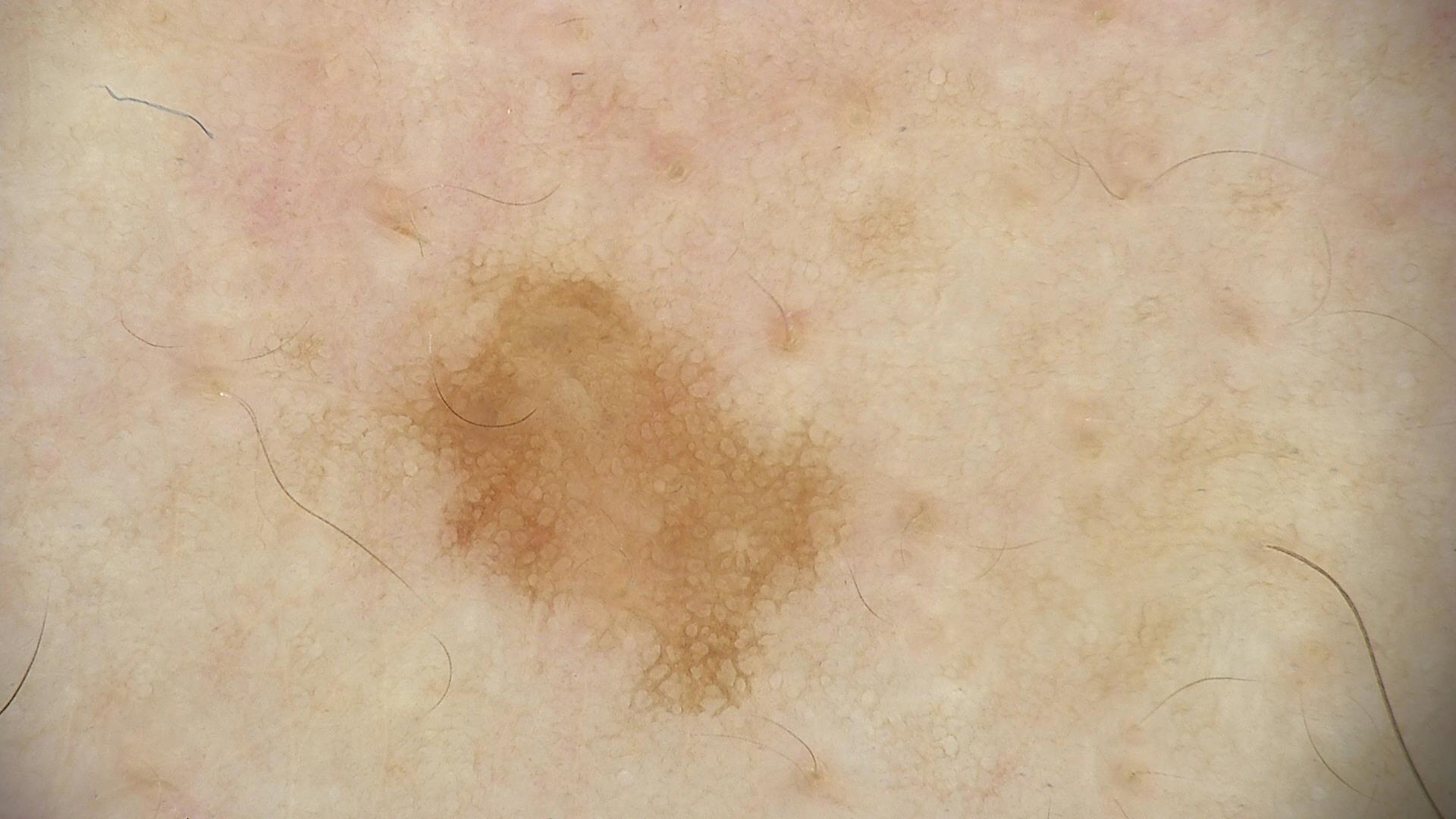diagnostic label: solar lentigo (expert consensus).